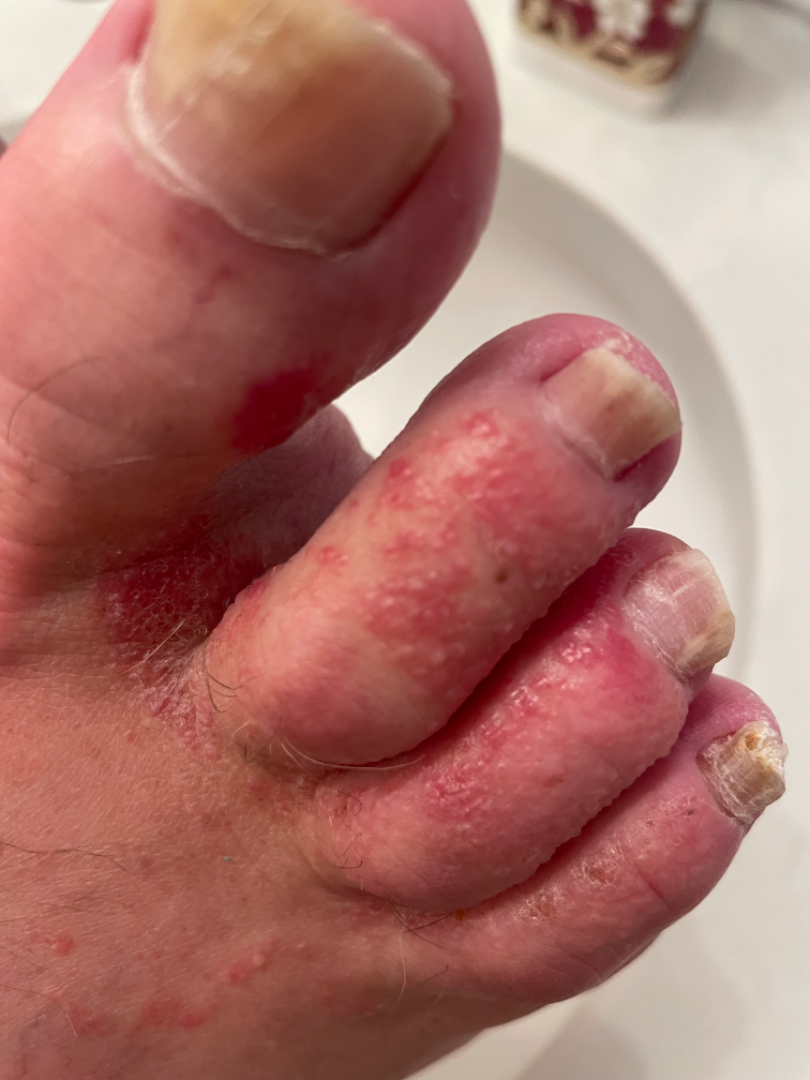Findings:
- framing — close-up
- assessment — the primary impression is Allergic Contact Dermatitis; also on the differential is Candida intertrigo; also raised was Eczema